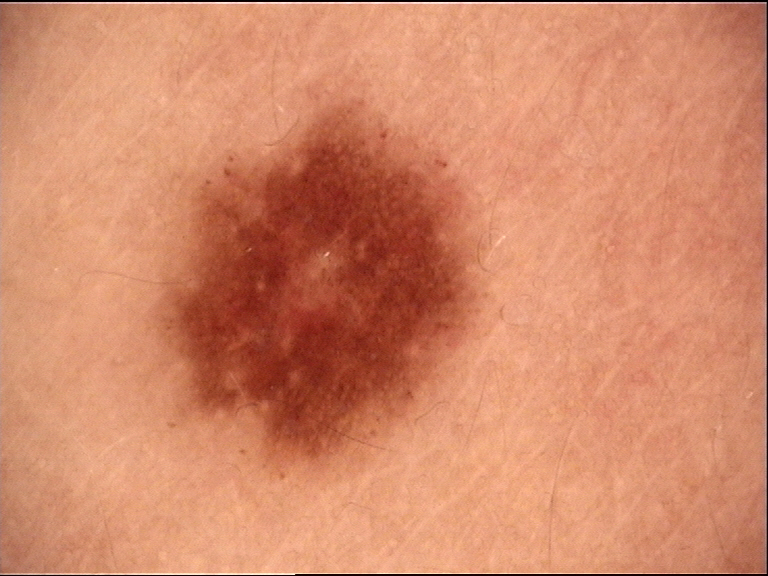Impression: The diagnosis was a dysplastic junctional nevus.